The front of the torso is involved. The patient described the issue as a rash. Reported duration is less than one week. The photograph is a close-up of the affected area. Symptoms reported: itching. The patient reports the lesion is rough or flaky and flat. The contributor is male.
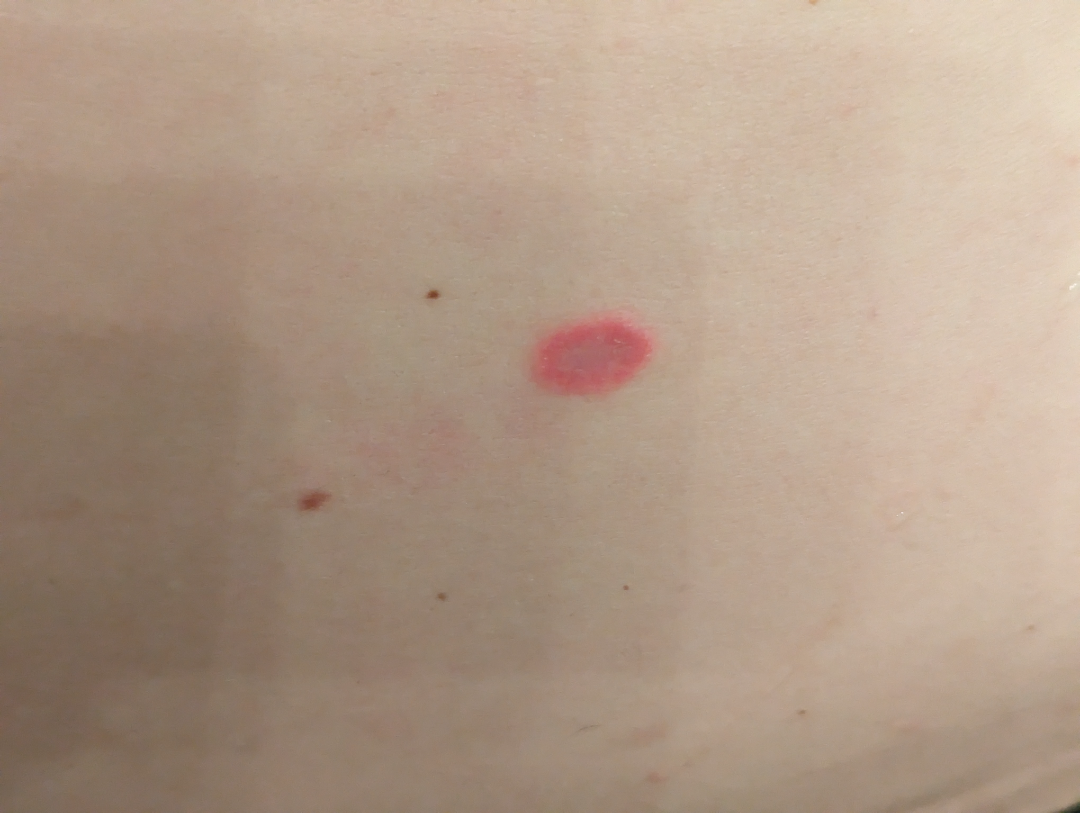assessment — not assessable.